A dermoscopic image of a skin lesion.
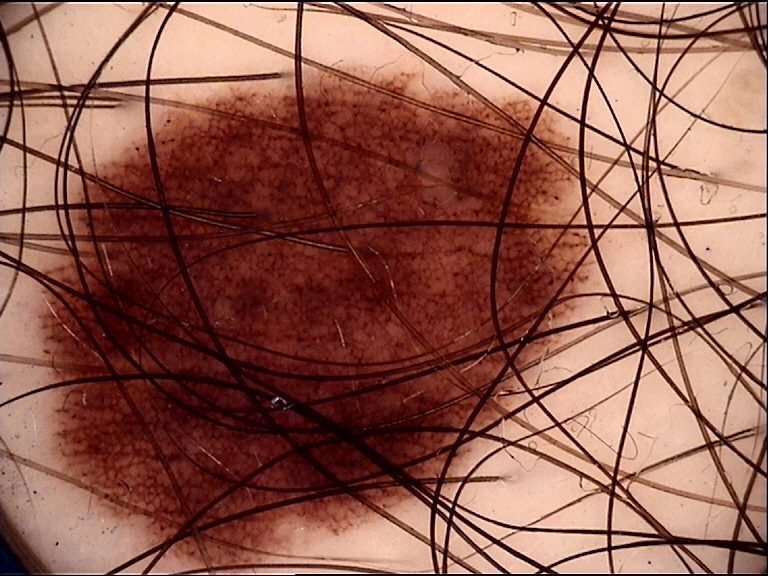{"diagnosis": {"name": "dysplastic junctional nevus", "code": "jd", "malignancy": "benign", "super_class": "melanocytic", "confirmation": "expert consensus"}}